A dermoscopic close-up of a skin lesion.
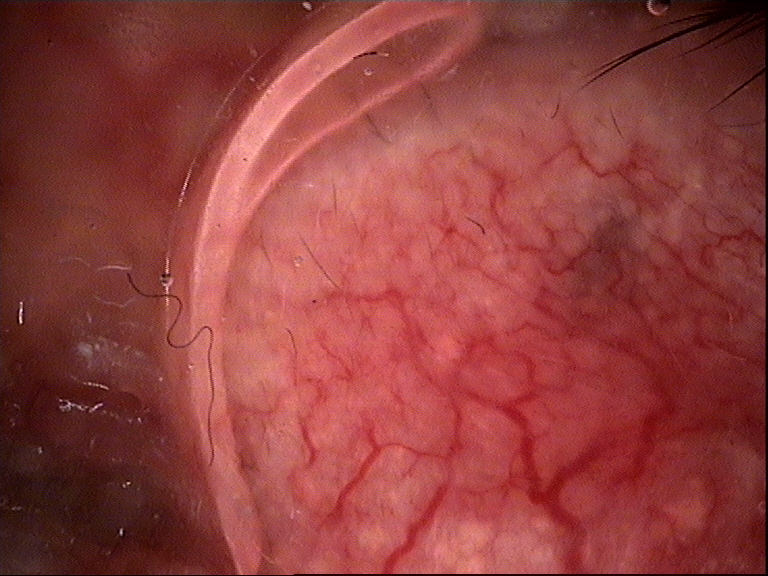Histopathology confirmed a basal cell carcinoma.